The patient says their skin reddens painfully with sun exposure. The patient describes having a moderate number of moles. A female patient 55 years of age — 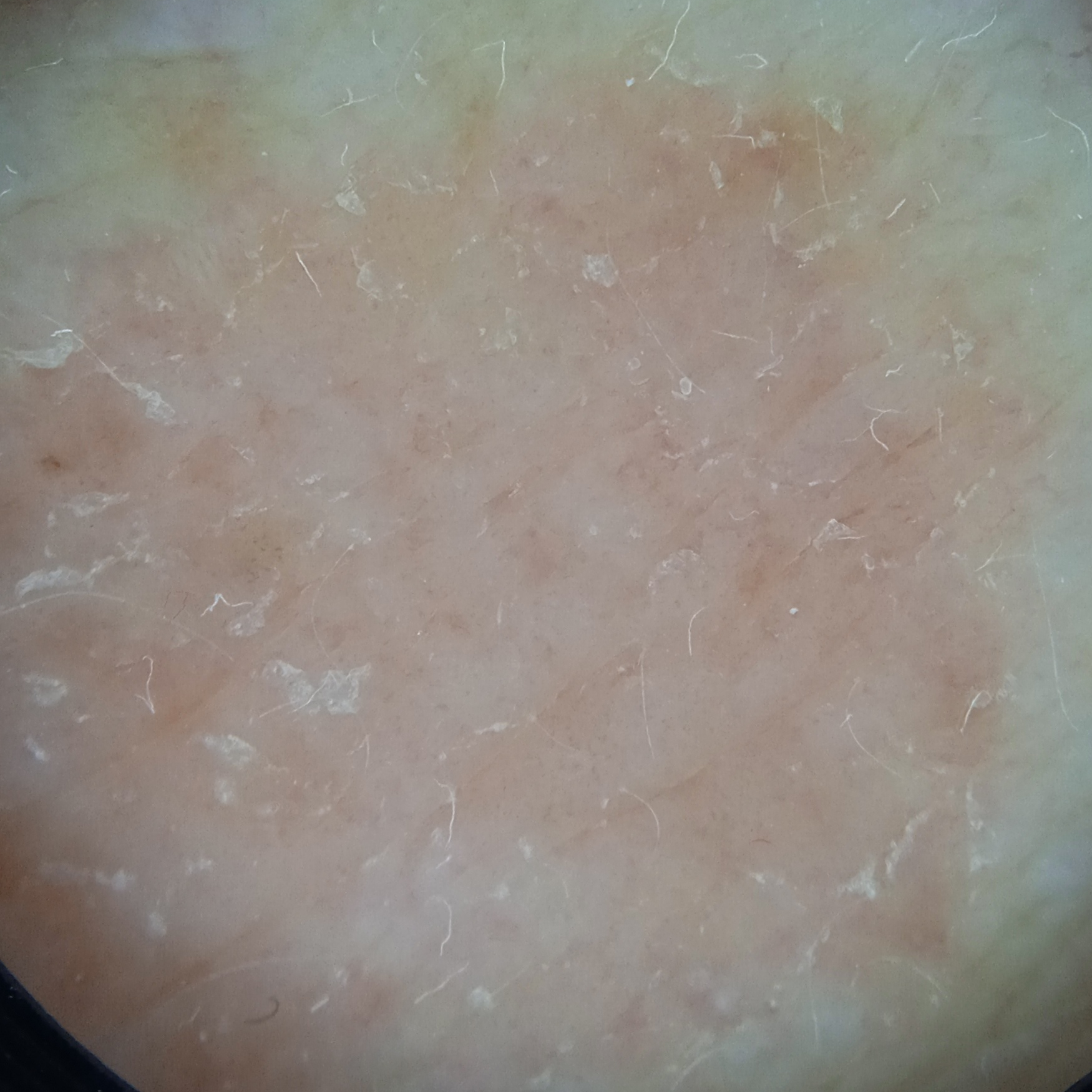• lesion size: 13.2 mm
• diagnosis: basal cell carcinoma (dermatologist consensus)